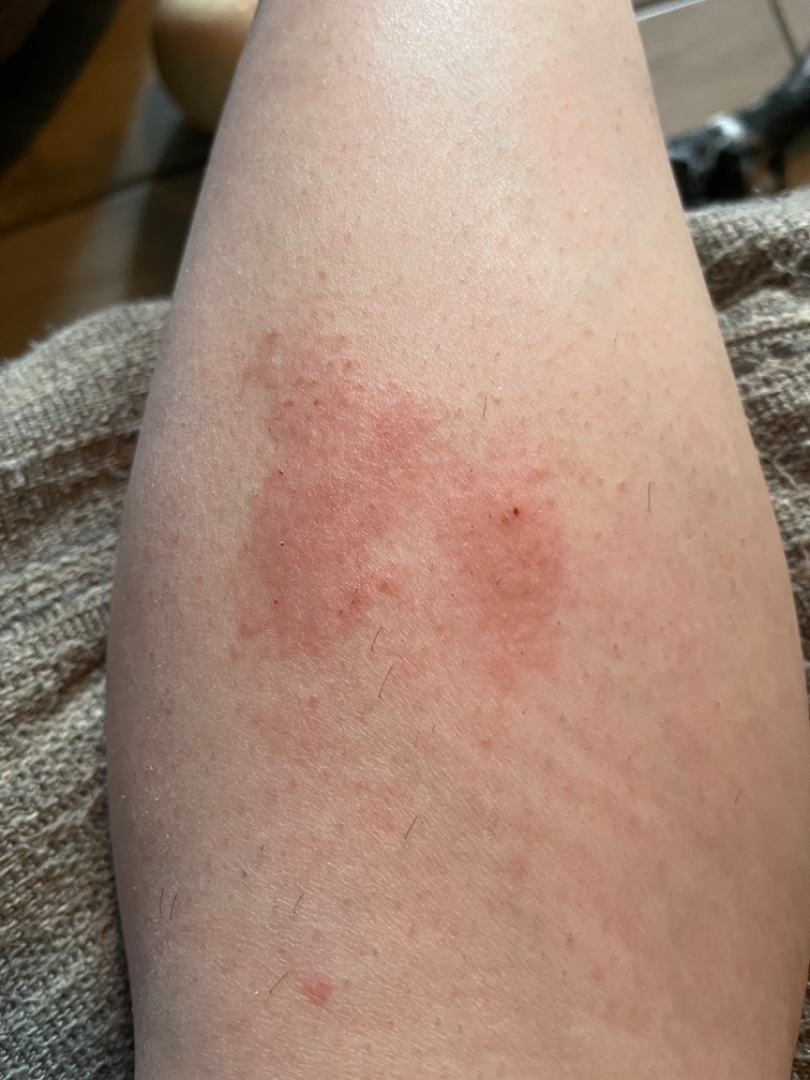Assessment:
The image was not sufficient for the reviewer to characterize the skin condition.
Clinical context:
A close-up photograph.